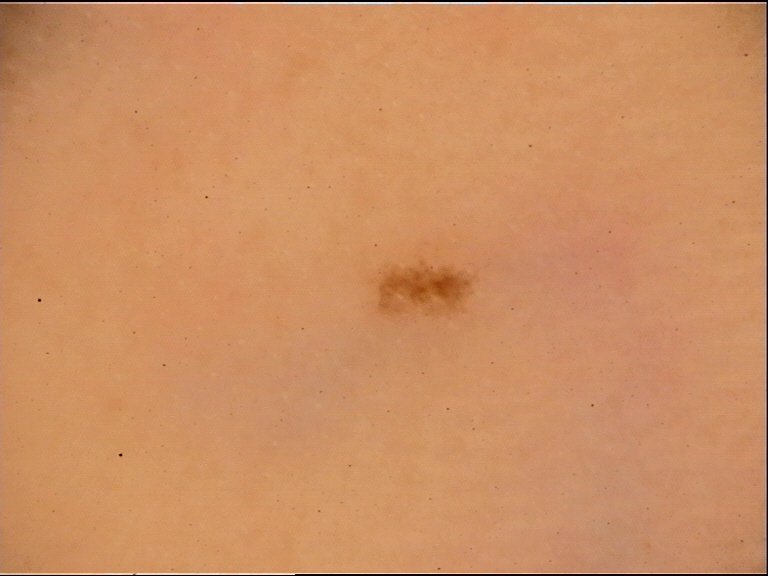– label — acral junctional nevus (expert consensus)